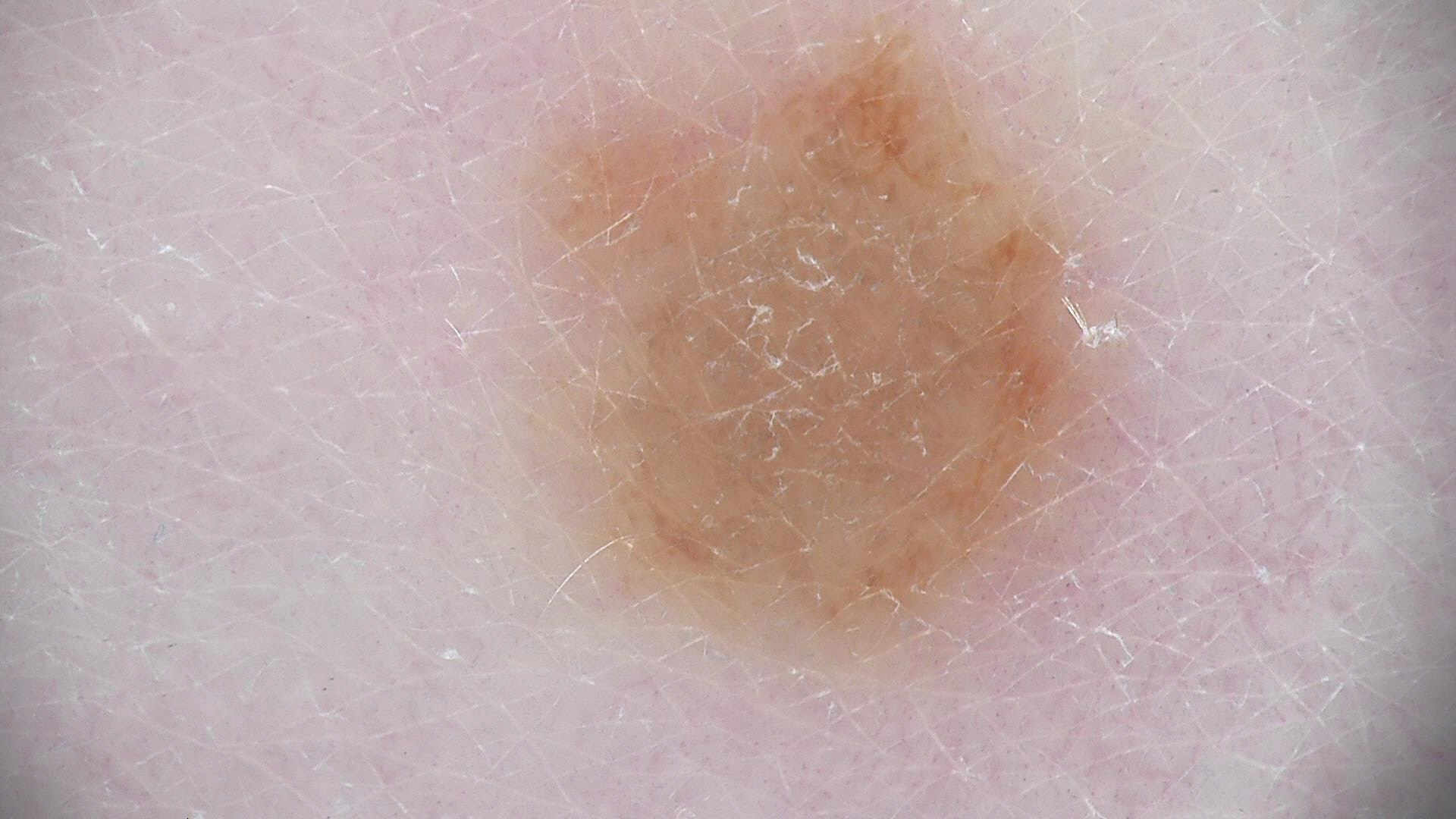Findings:
A dermoscopic image of a skin lesion.
Impression:
Diagnosed as a banal lesion — a dermal nevus.